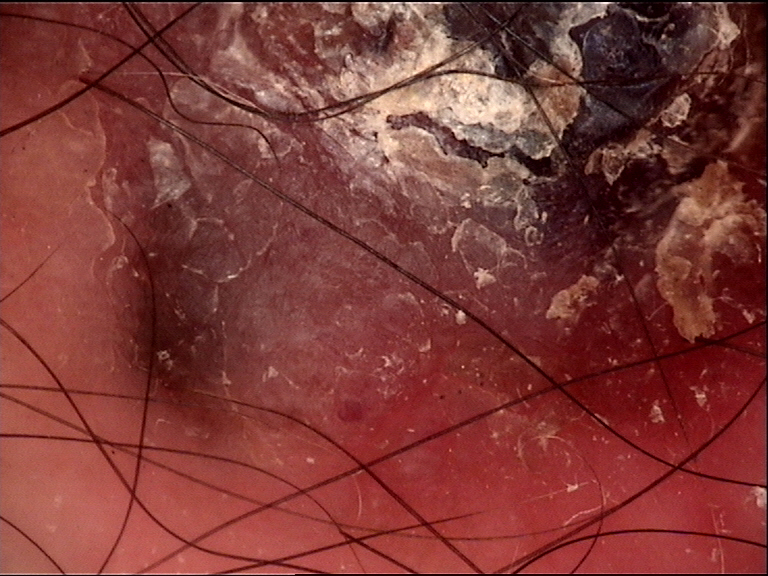modality: dermatoscopy, diagnostic label: melanoma (biopsy-proven).